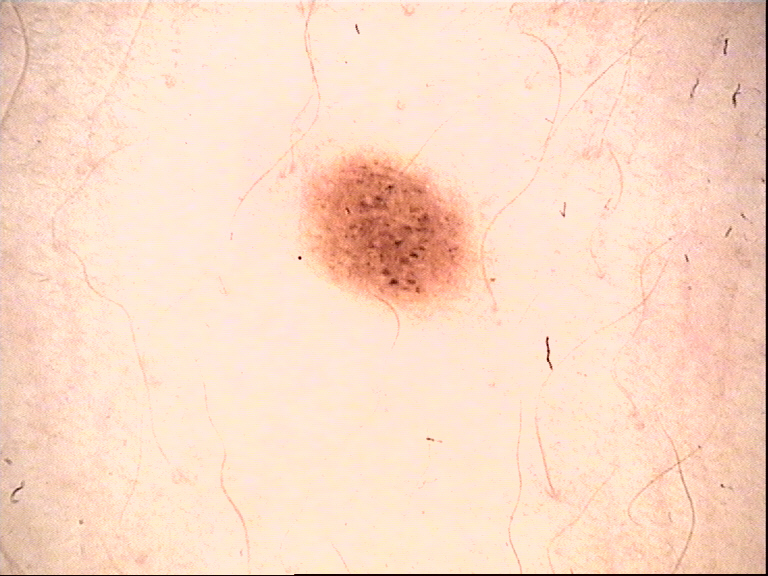Findings:
A dermoscopic close-up of a skin lesion.
Impression:
Labeled as a dysplastic junctional nevus.